Skin tone: Fitzpatrick V; lay graders estimated Monk Skin Tone 6 (US pool) or 3 (India pool). The photo was captured at a distance:
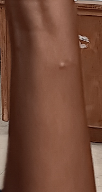The primary impression is Cyst.